A dermoscopic close-up of a skin lesion.
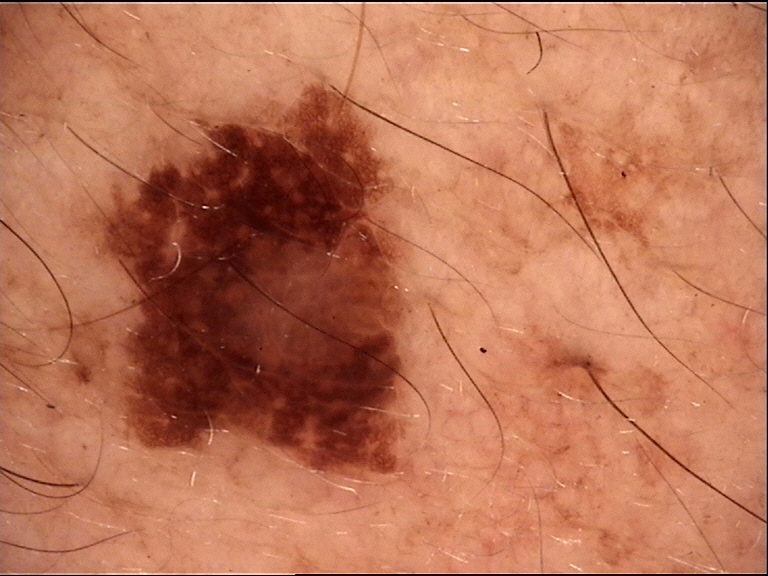The biopsy diagnosis was a lentigo maligna.